The patient is 18–29, male · the photograph is a close-up of the affected area: 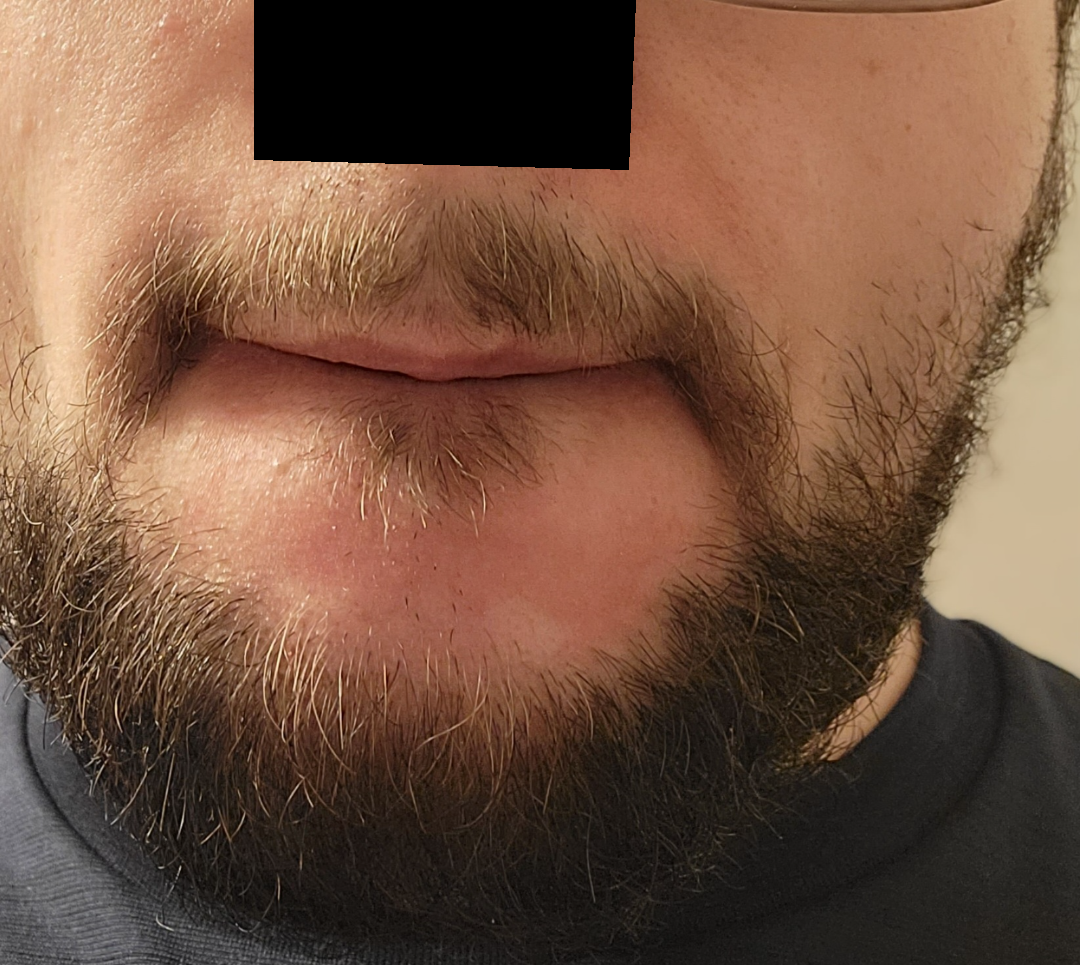{
  "differential": "Seborrheic Dermatitis"
}